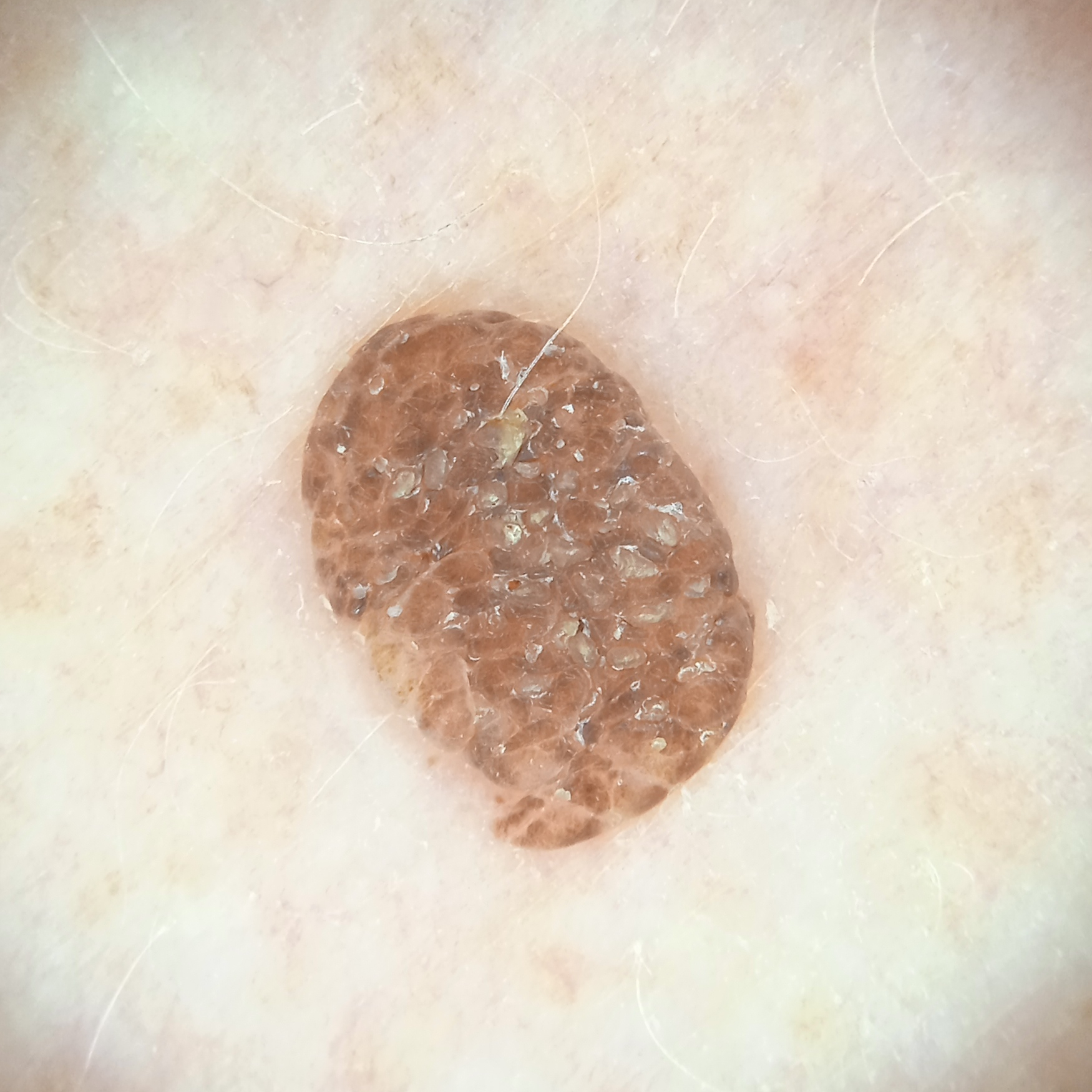| field | value |
|---|---|
| patient | female, 78 years of age |
| clinical context | research study (no referral diagnosis) |
| sun reaction | skin tans without first burning |
| anatomic site | an arm |
| diameter | 5.6 mm |
| diagnostic label | seborrheic keratosis (dermatologist consensus) |